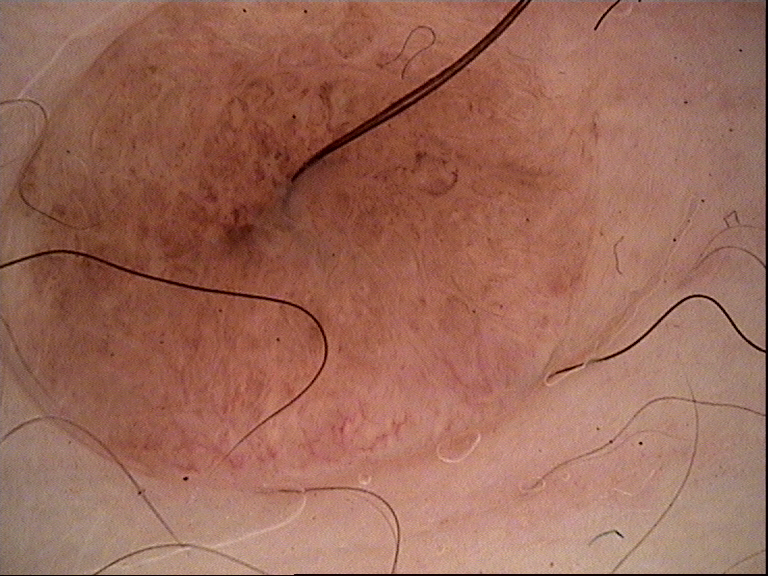A dermoscopic close-up of a skin lesion. The diagnostic label was a banal lesion — a dermal nevus.